A close-up photograph:
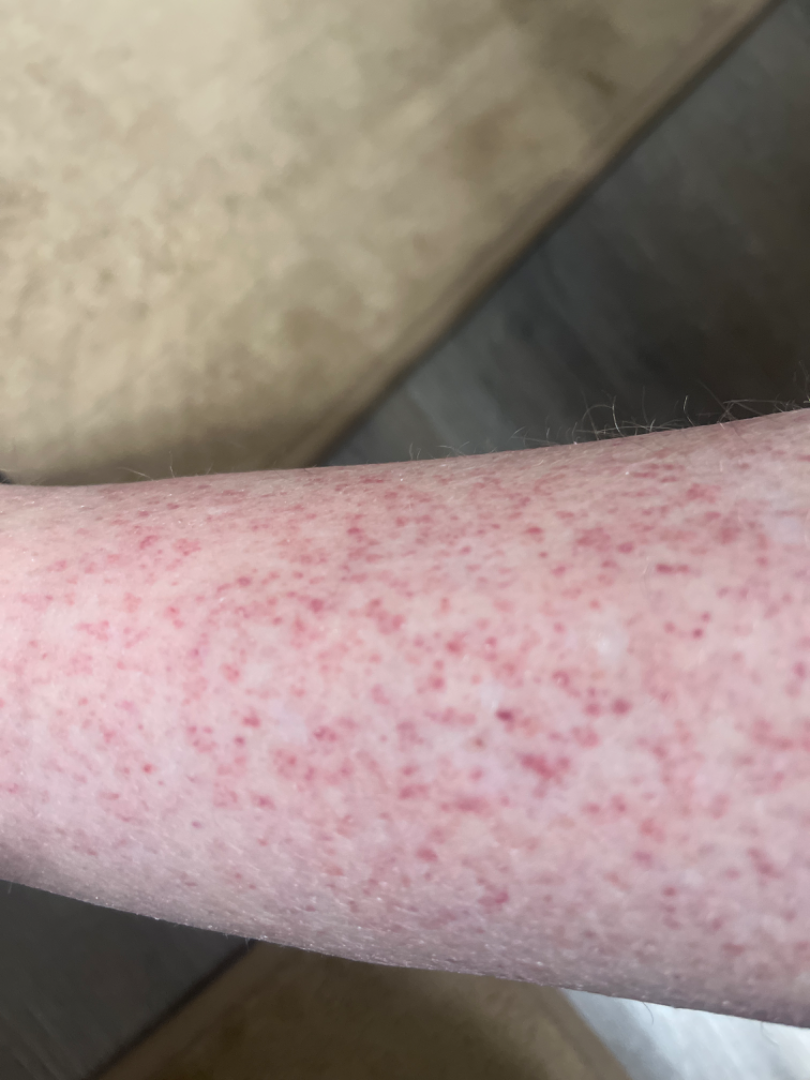Notes:
- impression — the differential is split between Folliculitis, Keratosis pilaris and Leukocytoclastic Vasculitis